The photograph was taken at a distance:
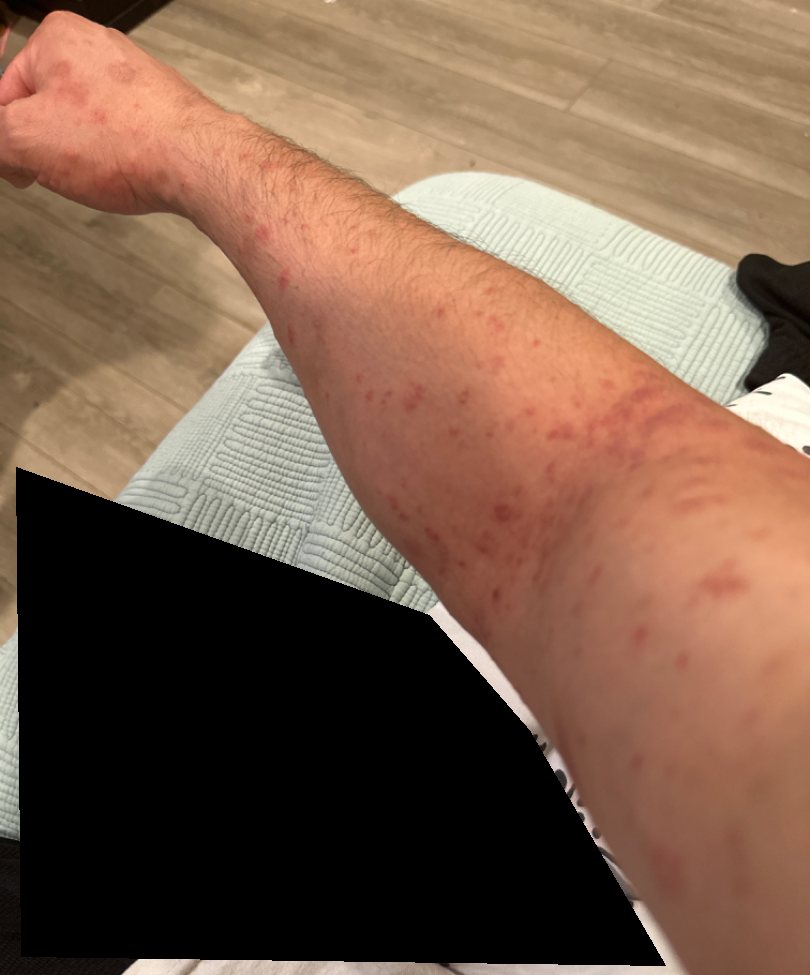| field | value |
|---|---|
| differential | Insect Bite (weight 0.67); Allergic Contact Dermatitis (weight 0.33) |